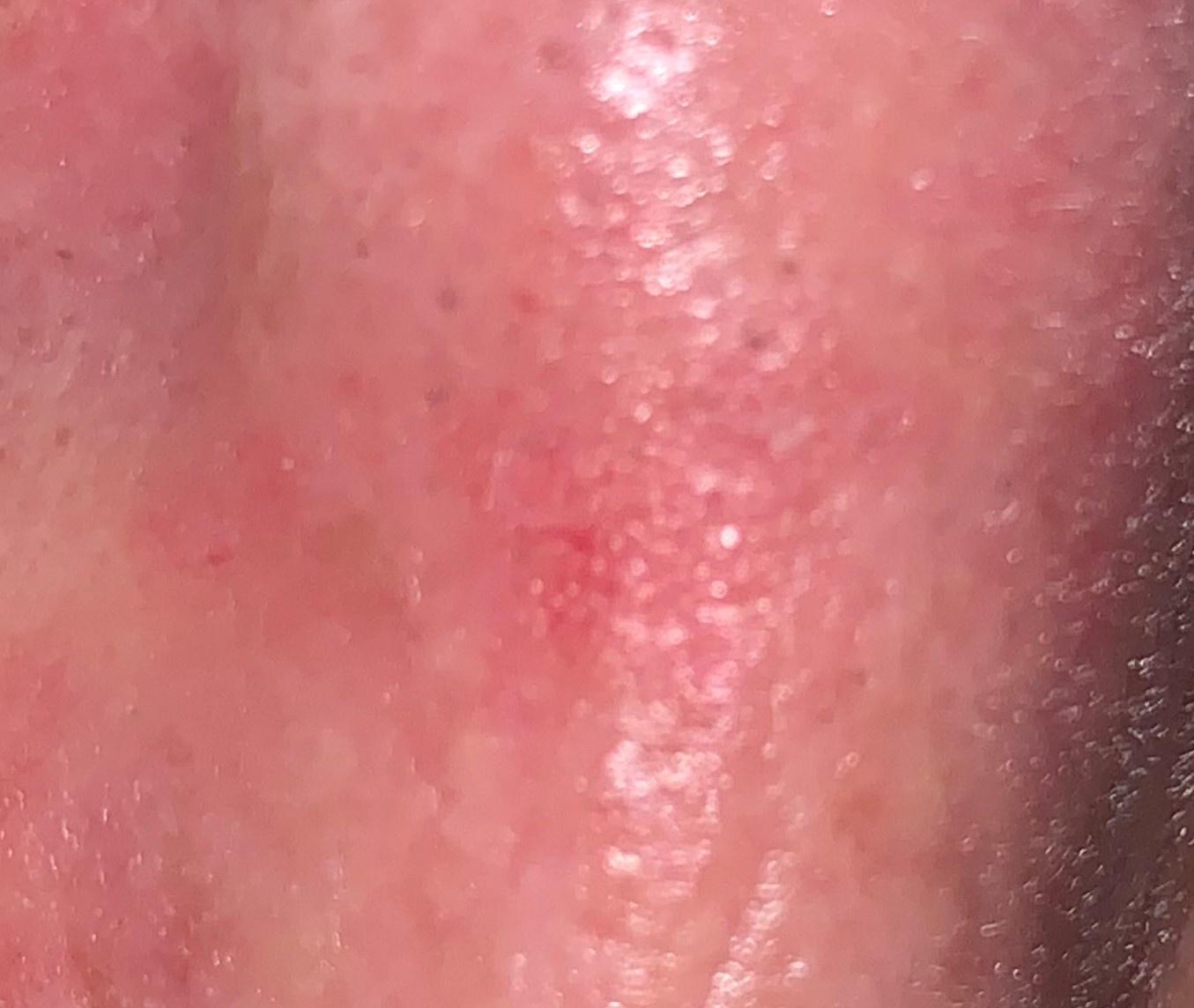skin_type: II
image: clinical photograph
patient:
  age_approx: 80
  sex: female
lesion_location:
  region: the head or neck
diagnosis:
  name: Solar or actinic keratosis
  malignancy: indeterminate
  confirmation: expert clinical impression
  lineage: epidermal